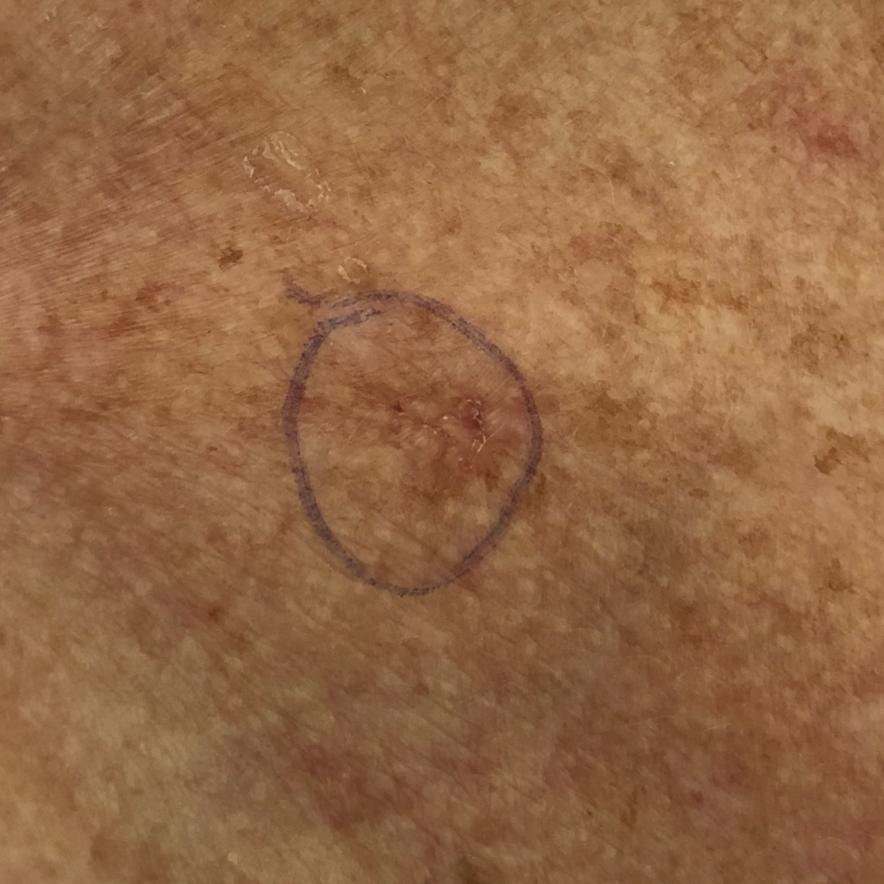Case:
* skin type: III
* imaging: clinical photo
* risk factors: prior skin cancer (patient or family), prior malignancy (patient or family), alcohol use, no tobacco use
* subject: female, 55 years of age
* body site: the chest
* lesion size: 5 × 4 mm
* patient-reported symptoms: itching
* diagnosis: actinic keratosis (clinical consensus)